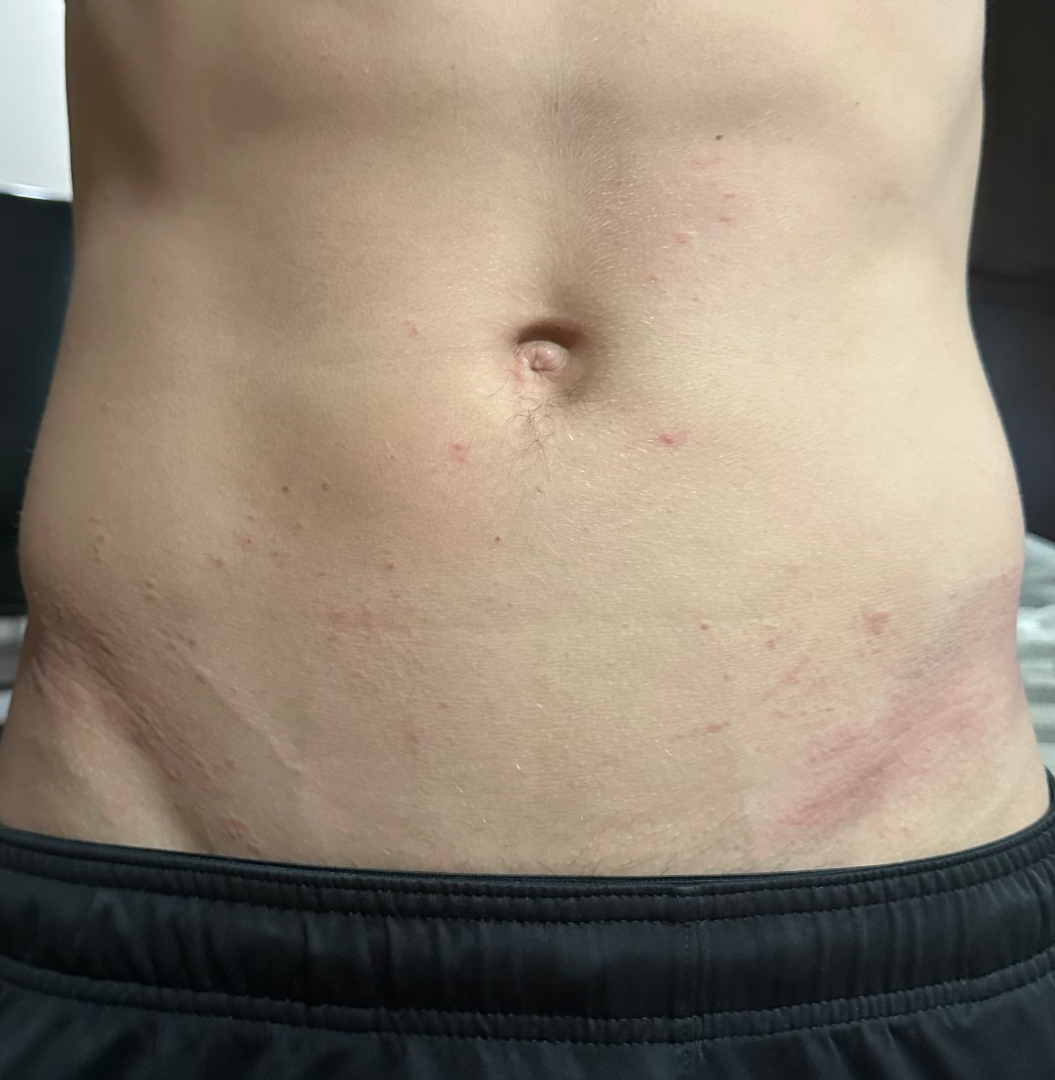| key | value |
|---|---|
| assessment | unable to determine |
| photo taken | at a distance |
| anatomic site | back of the torso, leg and front of the torso |
| patient's own categorization | a rash |
| texture | raised or bumpy |
| reported symptoms | itching |
| contributor | male, age 18–29 |
| onset | one to four weeks |